A dermoscopic photograph of a skin lesion:
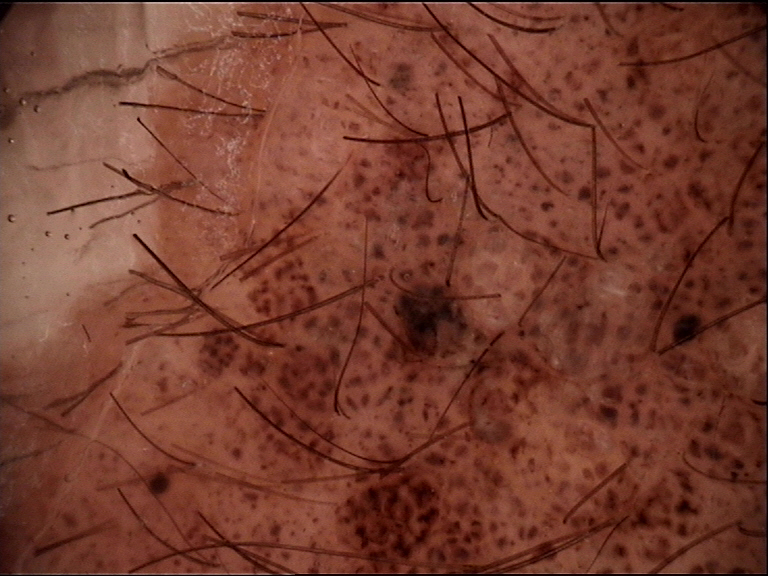category: banal; diagnostic label: congenital compound nevus (expert consensus).